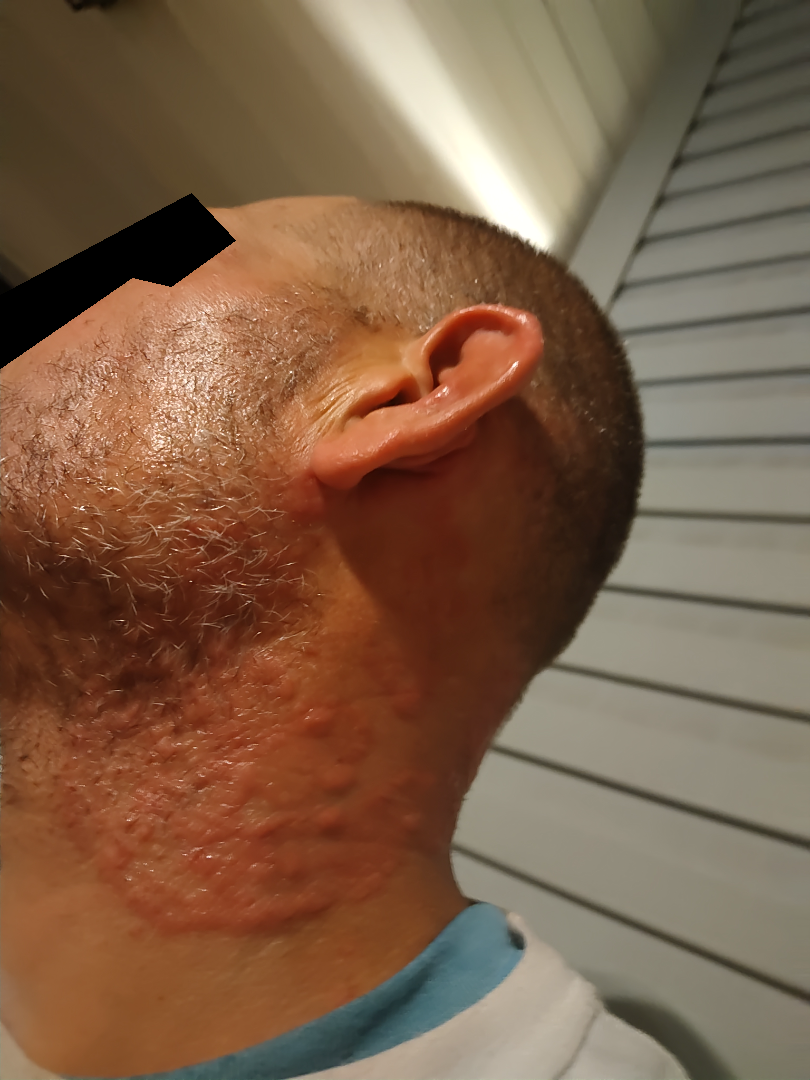The photograph was taken at a distance. The primary impression is Granuloma annulare.